Acquired for a research image collection, with no referral diagnosis. A dermoscopy image of a skin lesion: 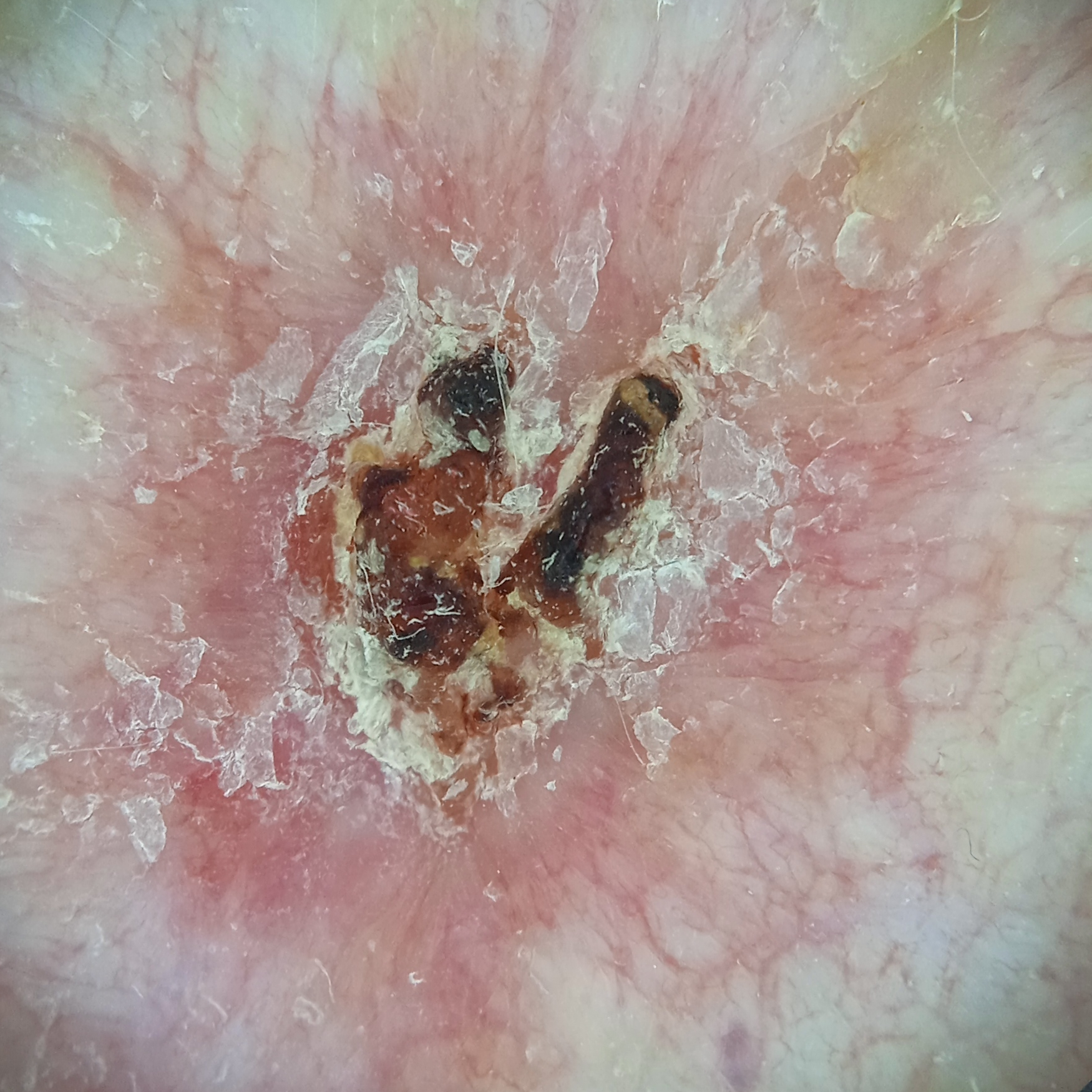The lesion is on the back.
The lesion measures approximately 9.5 mm.
The diagnostic impression was a basal cell carcinoma.